A skin lesion imaged with a dermatoscope.
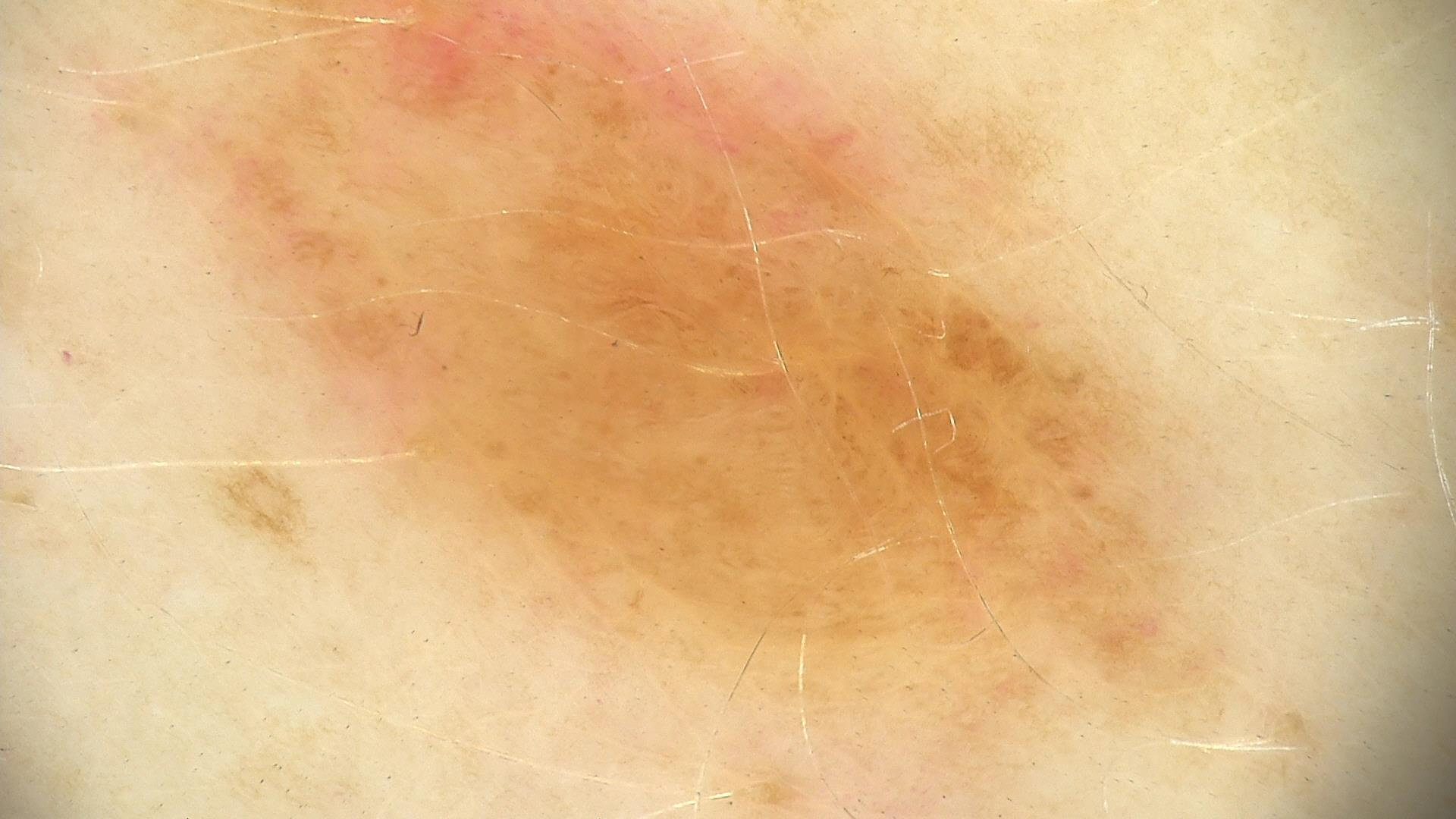{"diagnosis": {"name": "junctional nevus", "code": "jb", "malignancy": "benign", "super_class": "melanocytic", "confirmation": "expert consensus"}}